A close-up photograph: 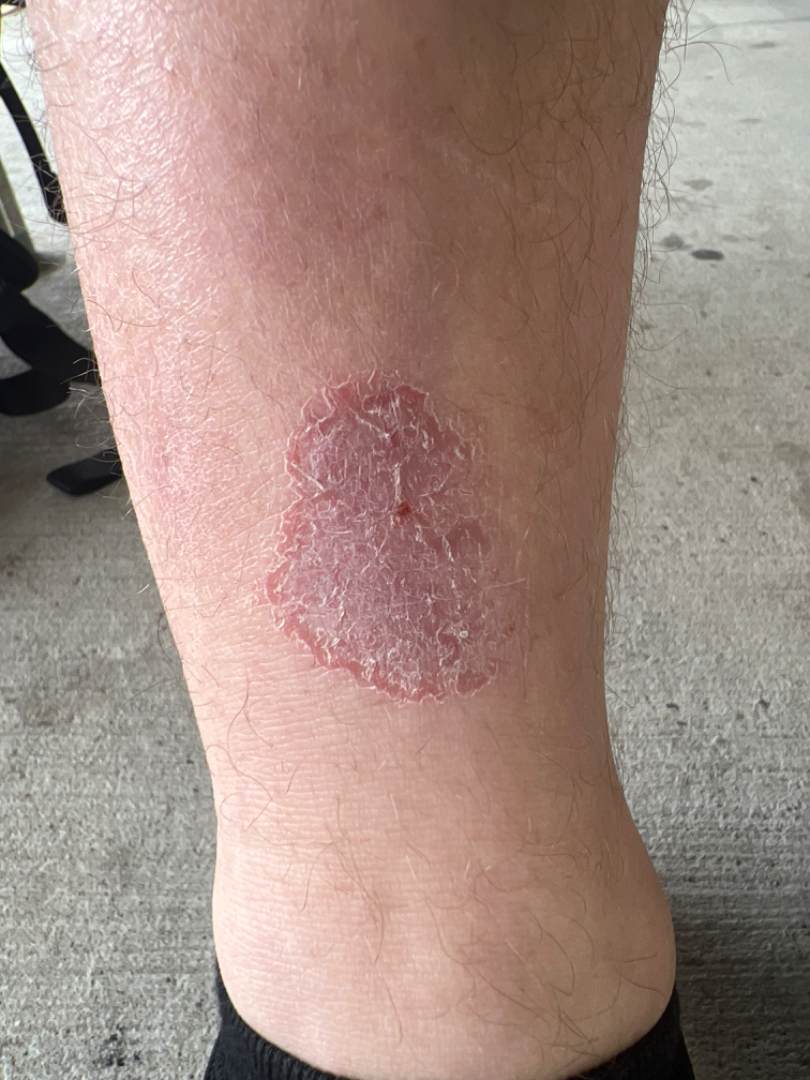assessment = Eczema and Acute and chronic dermatitis were each considered, in no particular order